A dermoscopy image of a single skin lesion.
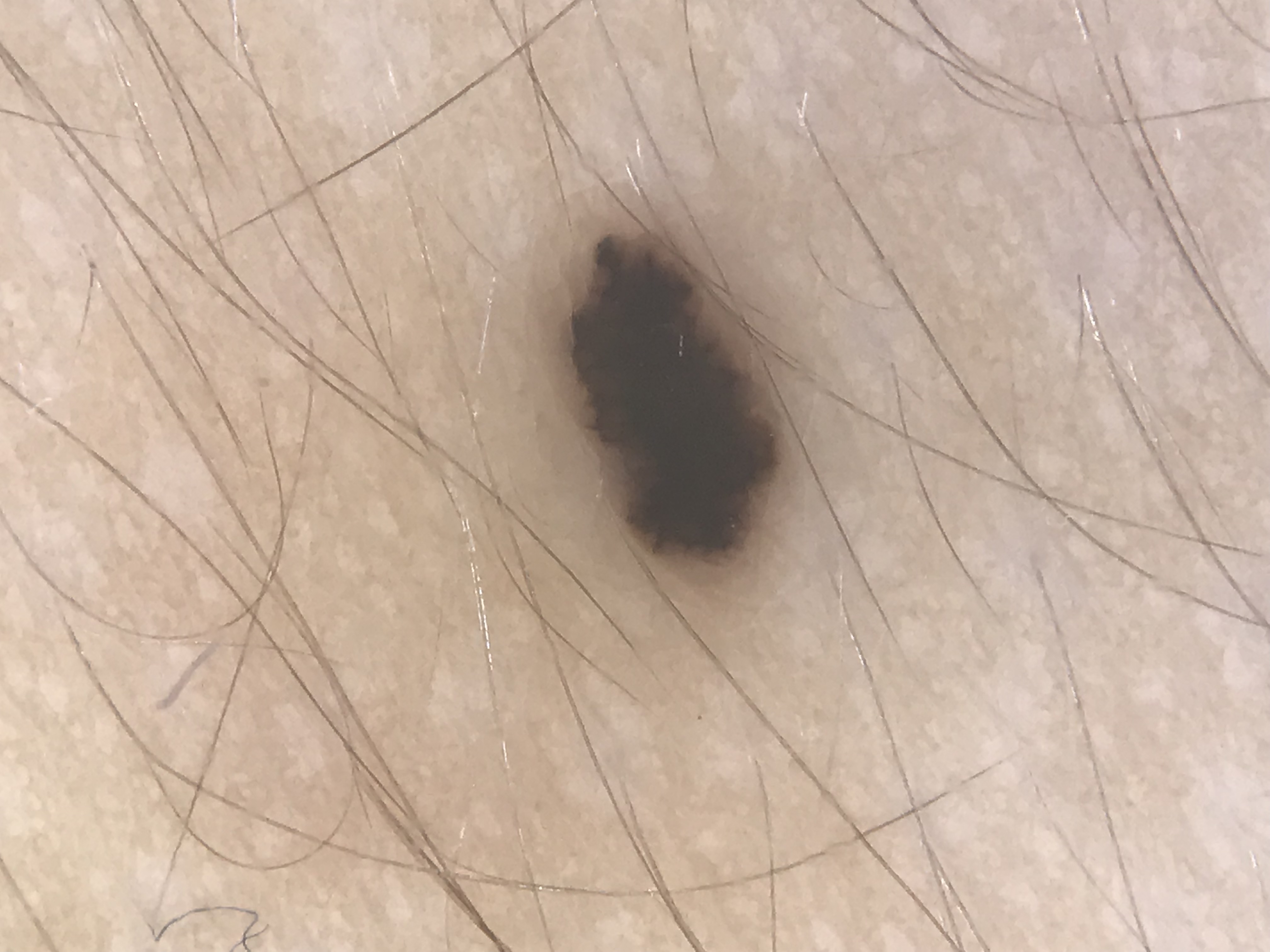assessment=dysplastic junctional nevus (expert consensus)